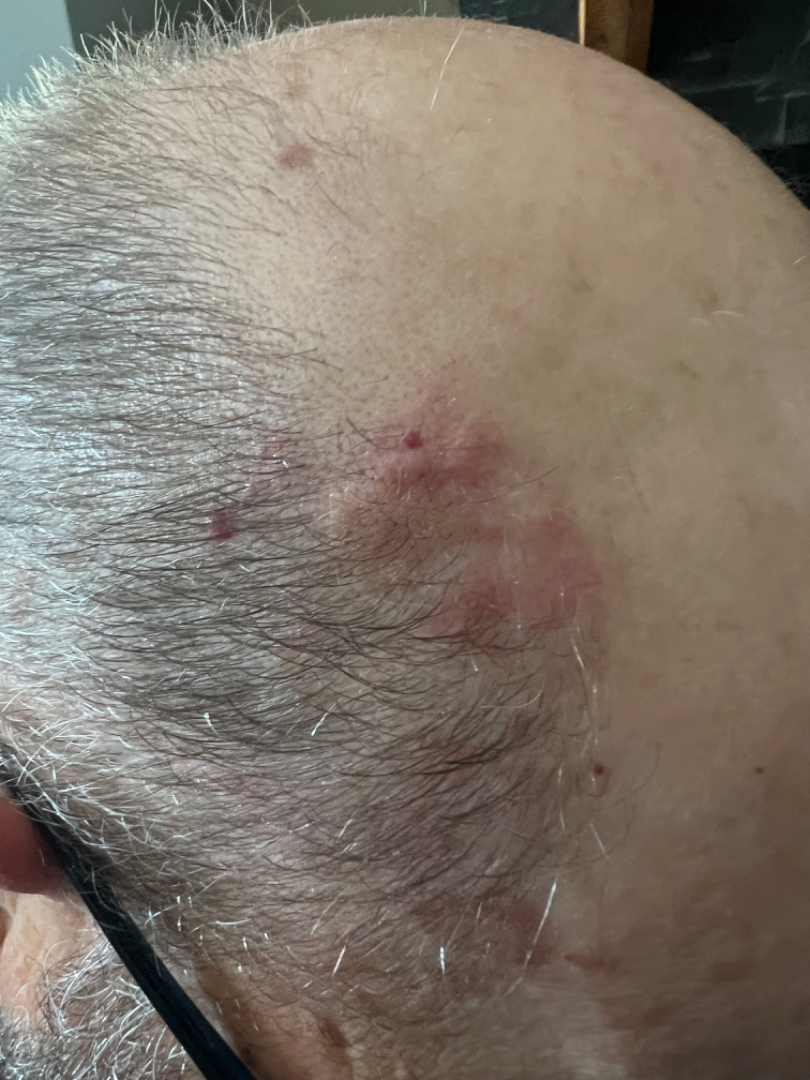shot type = close-up; subject = male, age 60–69; affected area = head or neck.